A skin lesion imaged with a dermatoscope.
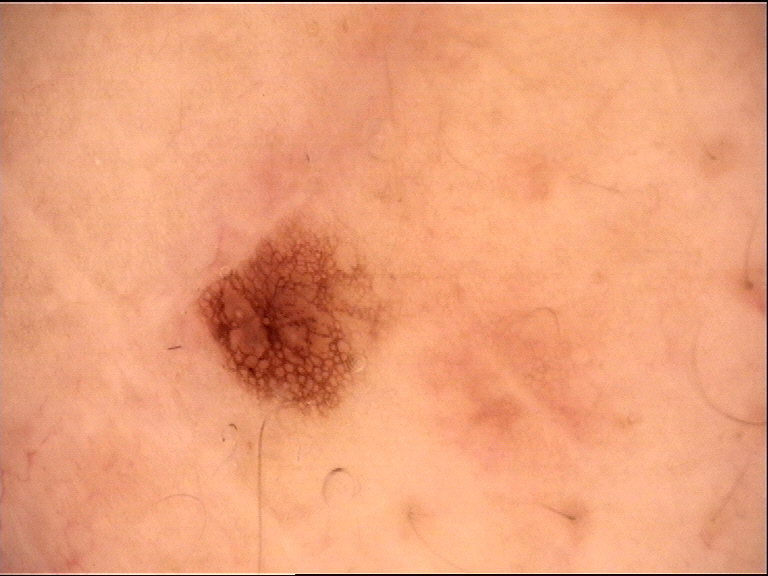Diagnosed as a dysplastic junctional nevus.